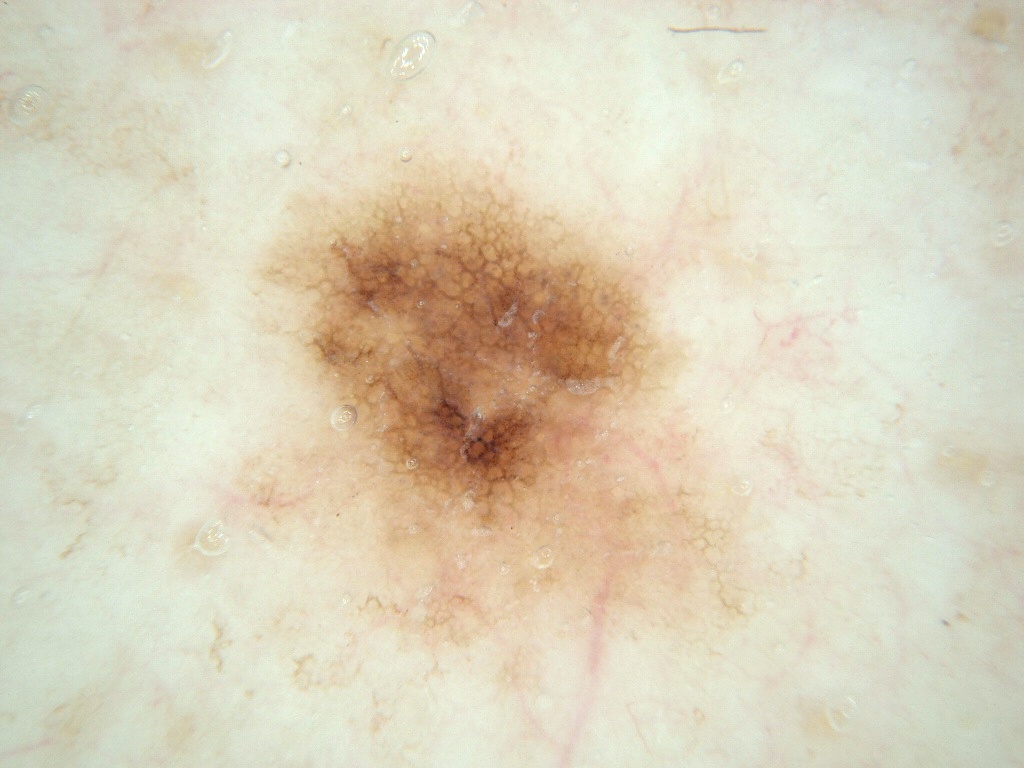image = dermoscopy of a skin lesion
patient = male, aged 83 or over
lesion size = ~22% of the field
features = pigment network; absent: milia-like cysts, globules, negative network, and streaks
location = left=236, top=151, right=749, bottom=652
impression = a melanocytic nevus